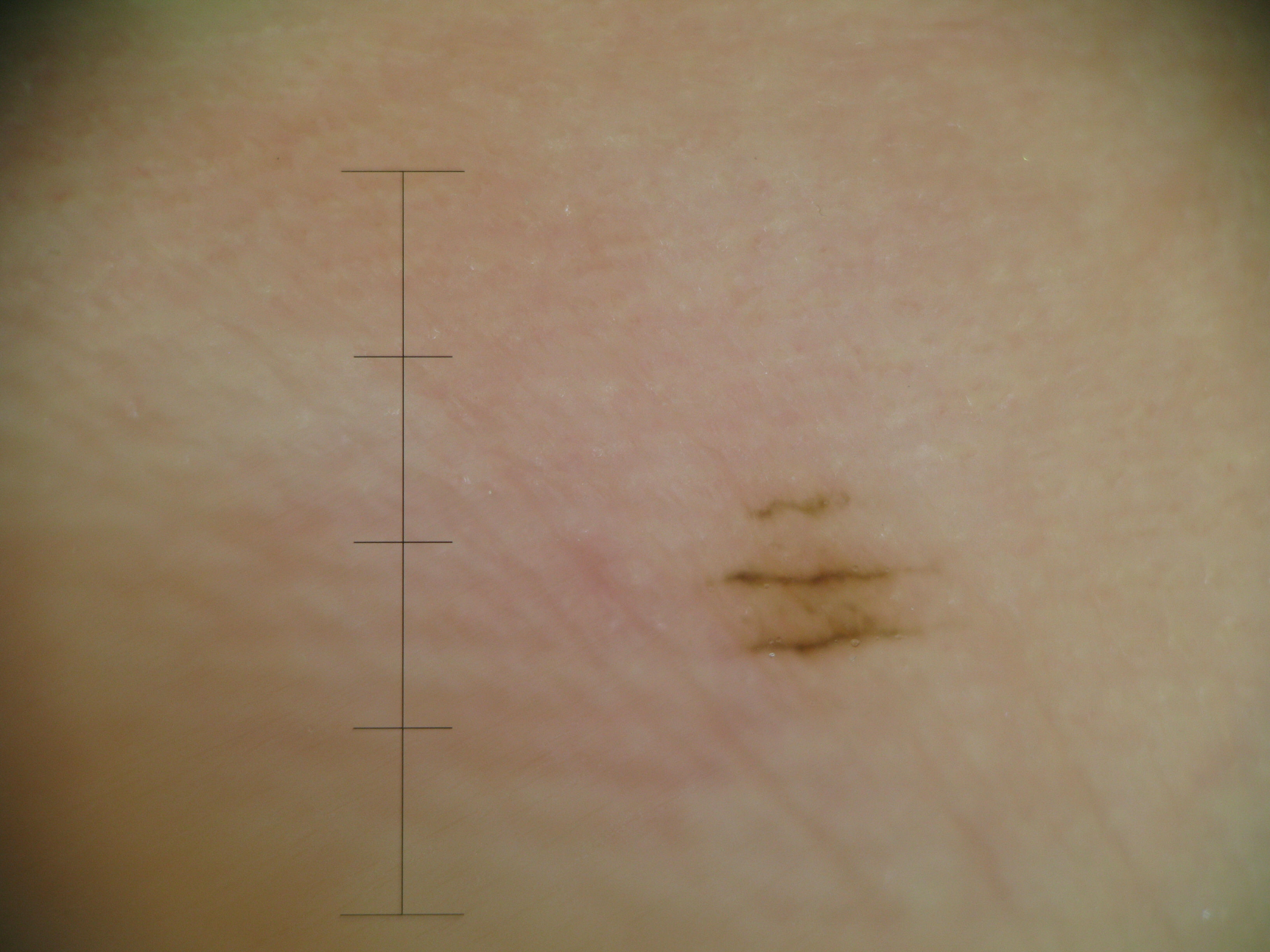Findings:
– image: dermoscopy
– assessment: acral junctional nevus (expert consensus)